A male patient aged around 60.
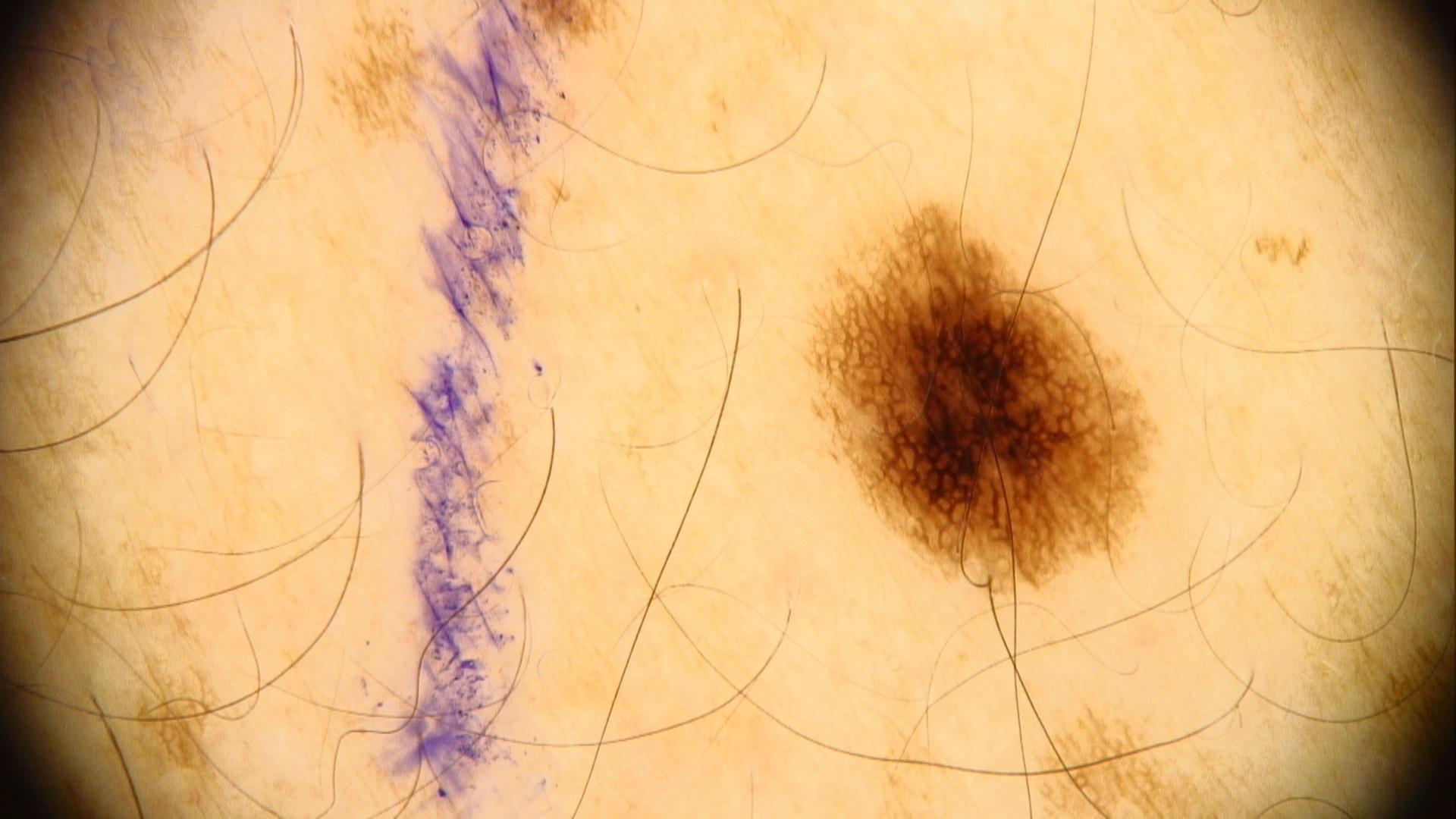Q: What is this lesion?
A: Nevus